A dermoscopic image of a skin lesion. Referred with a clinical suspicion of basal cell carcinoma. Few moles overall by the patient's own estimate. By self-report, a personal history of skin cancer, a personal history of cancer, no prior organ transplant, and no immunosuppression — 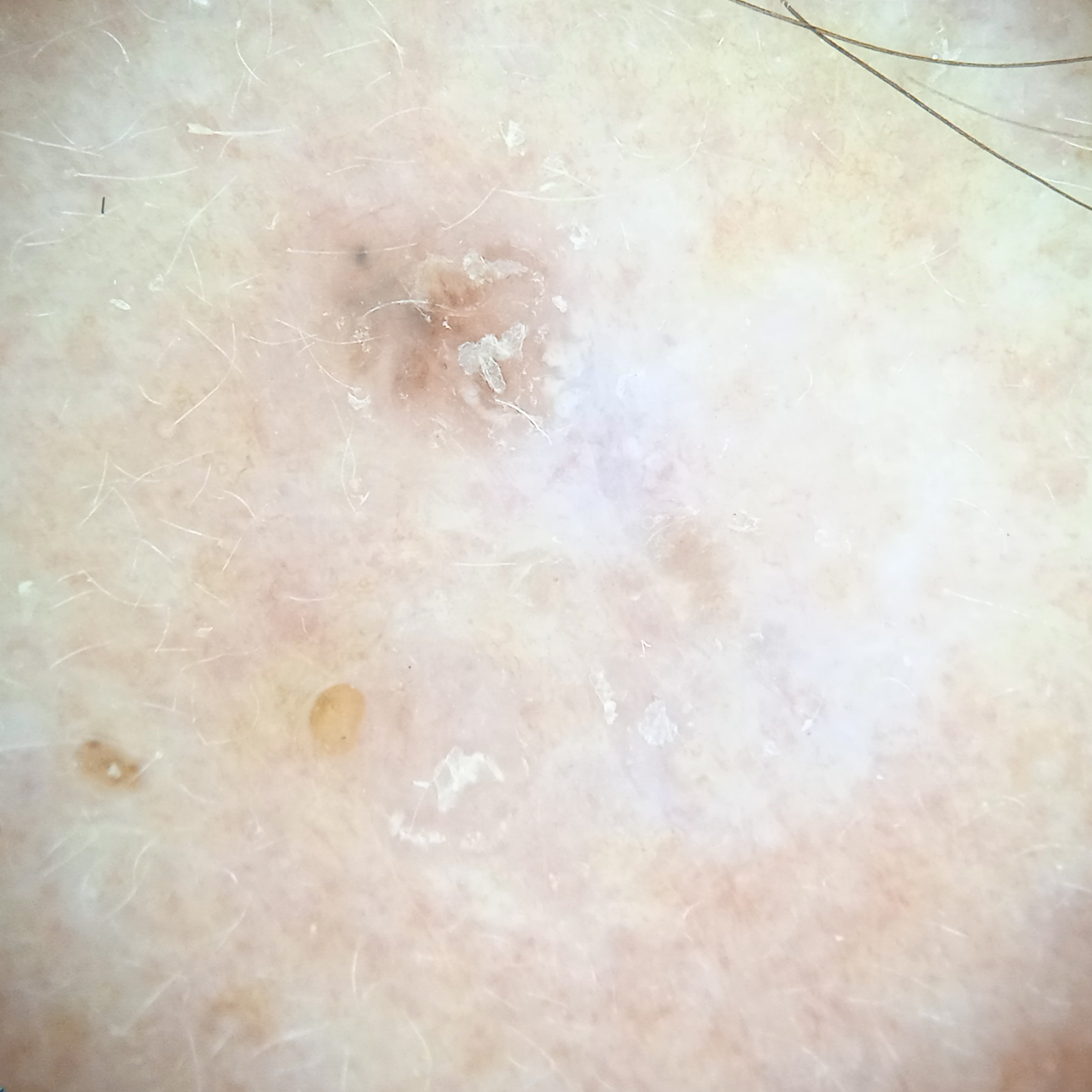lesion_size:
  diameter_mm: 6.6
diagnosis:
  name: basal cell carcinoma
  malignancy: malignant
  procedure: excision
  tumor_thickness_mm: 1.0